The affected area is the arm; the lesion is associated with bothersome appearance and itching; the patient considered this a rash; the condition has been present for less than one week; the lesion is described as raised or bumpy; male patient, age 18–29; the photo was captured at an angle.
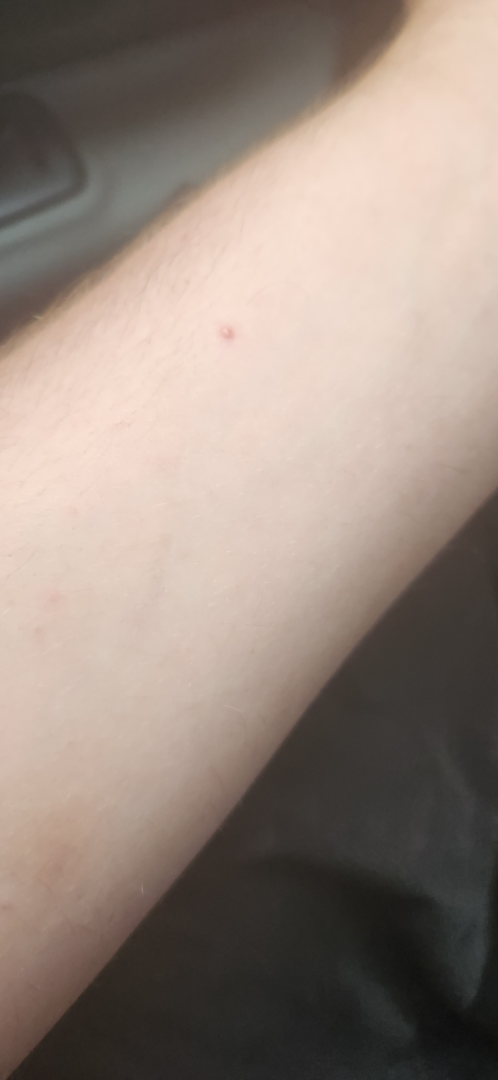The image was not sufficient for the reviewer to characterize the skin condition.